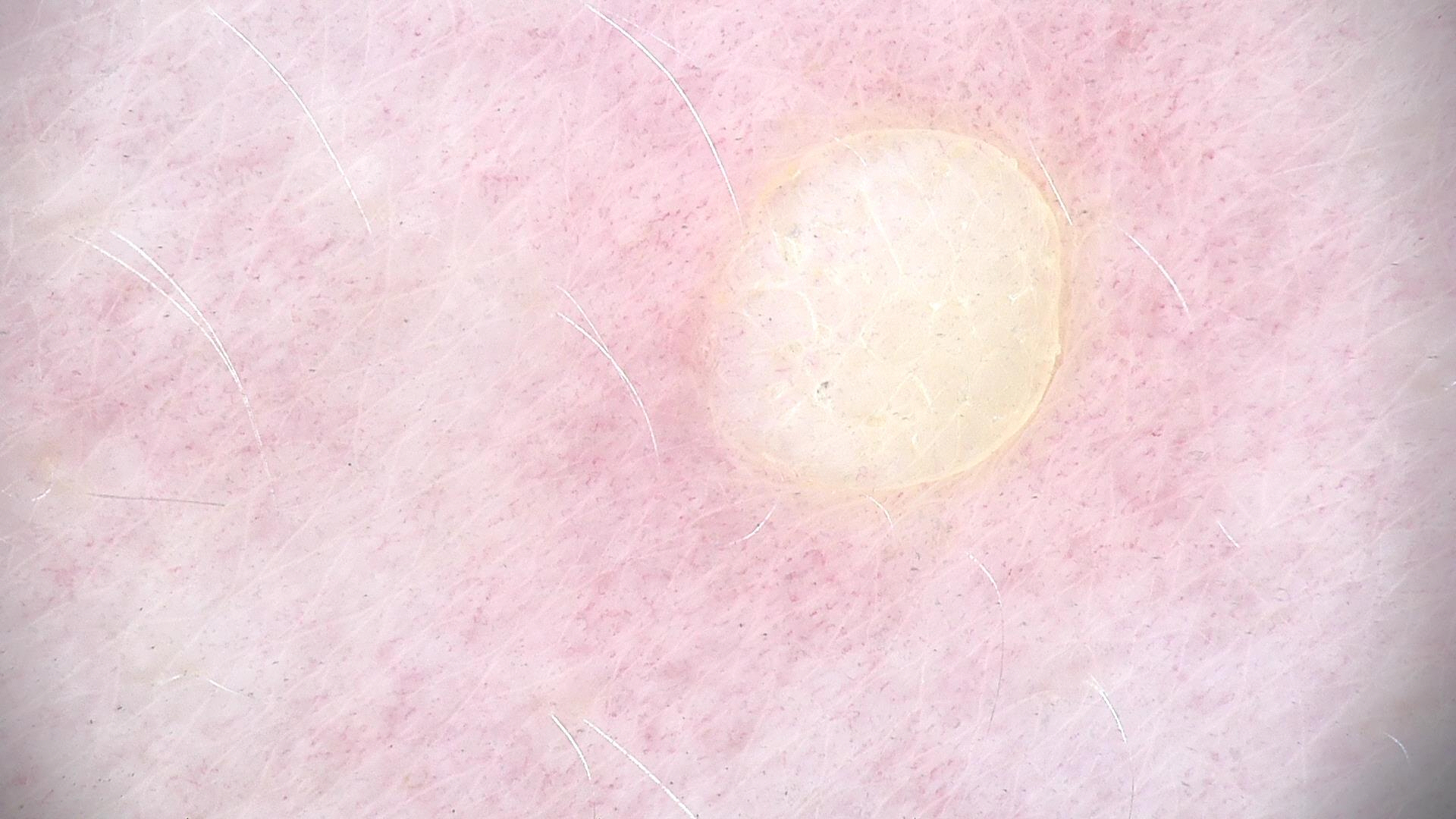A dermoscopic close-up of a skin lesion. The architecture is that of a banal lesion. The diagnostic label was a dermal nevus.